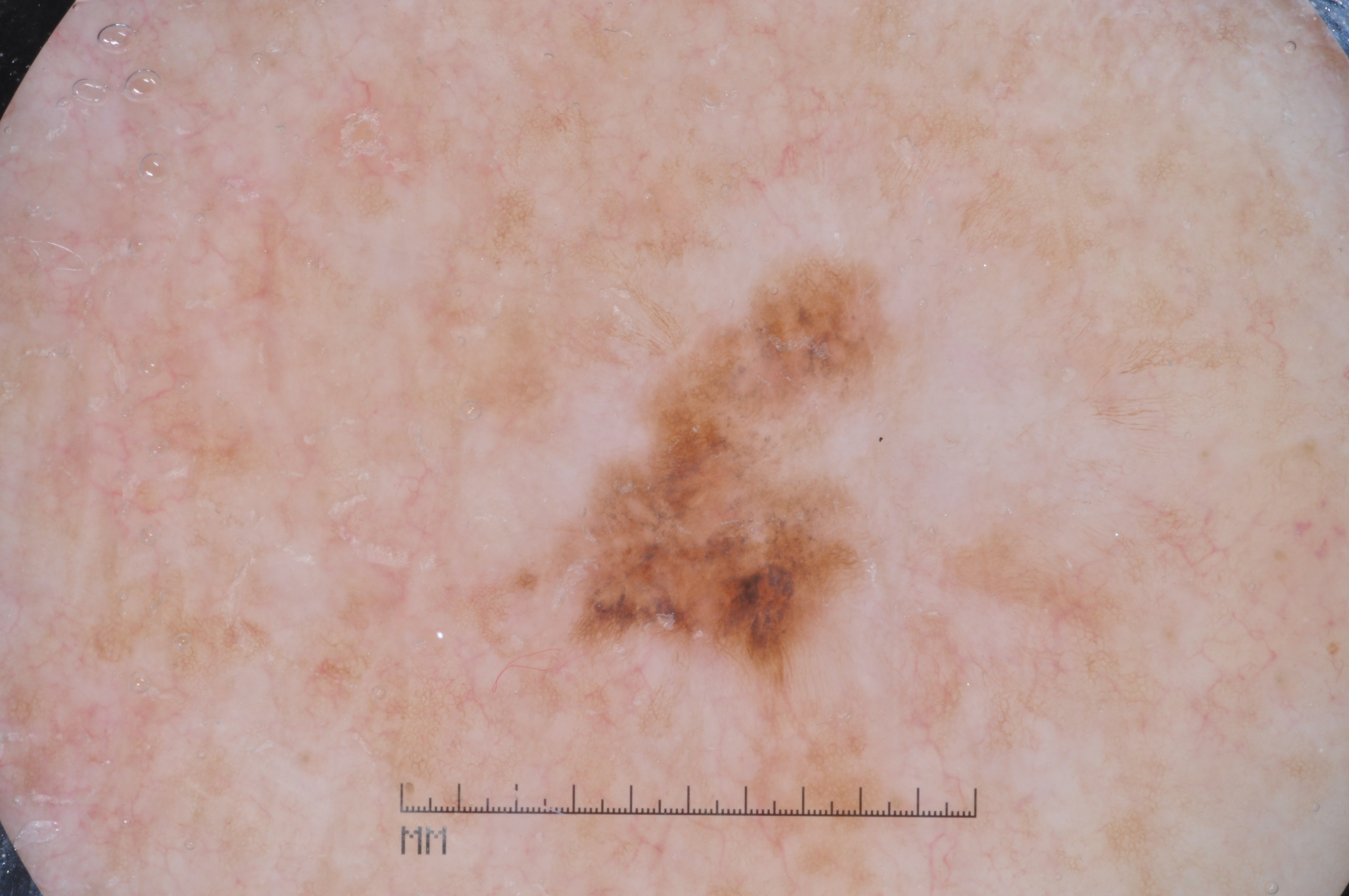This is a dermoscopic photograph of a skin lesion.
In (x1, y1, x2, y2) order, the lesion spans (461, 246, 928, 751).
Consistent with a melanocytic nevus, a benign lesion.